The patient notes the condition has been present for about one day. The patient considered this skin that appeared healthy to them. The patient is 50–59, male. The photo was captured at an angle. Texture is reported as flat. The affected area is the leg. Symptoms reported: bothersome appearance — 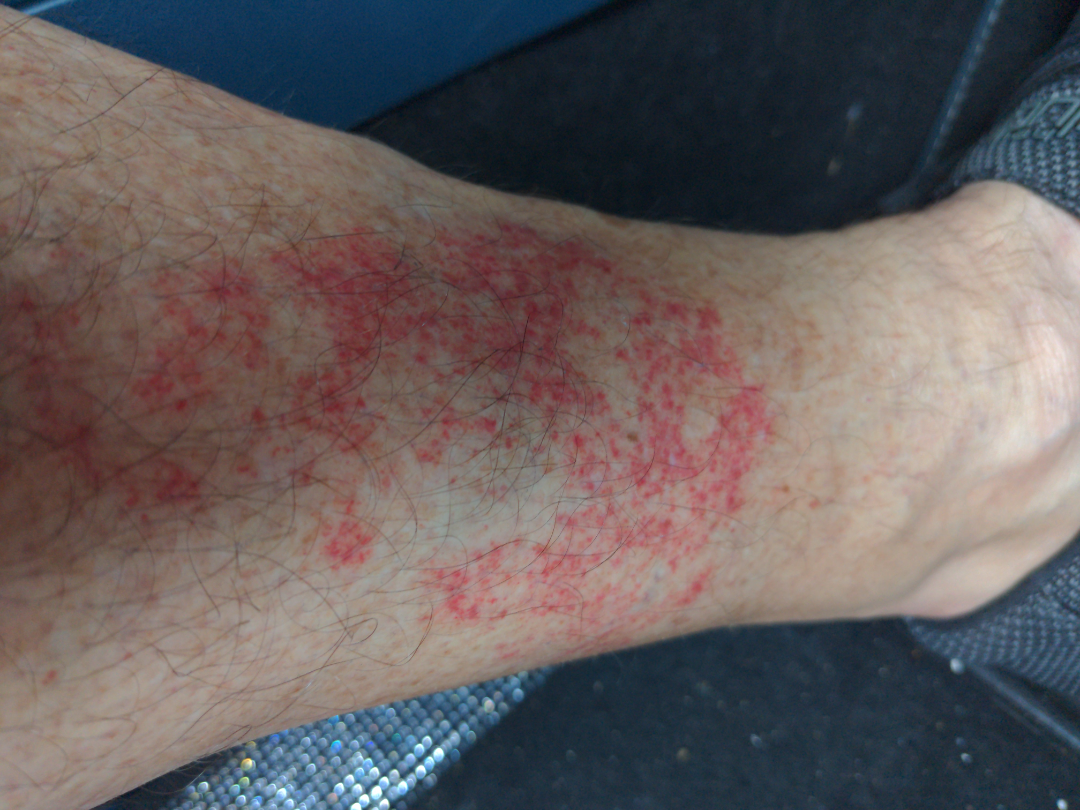Findings:
The skin findings could not be characterized from the image.